The subject is a female in their 70s; a dermatoscopic image of a skin lesion.
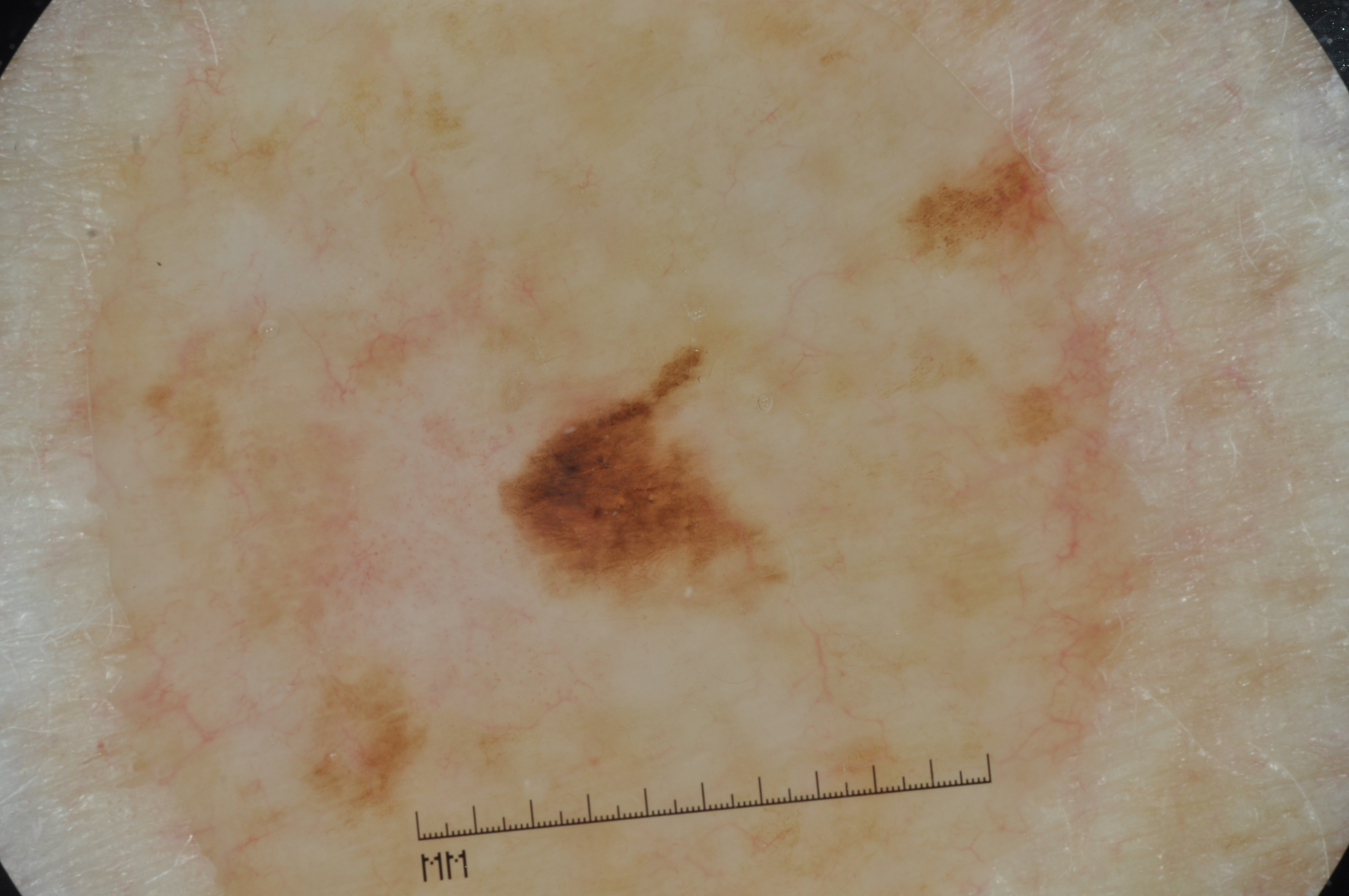On dermoscopy, the lesion shows pigment network and milia-like cysts, with no streaks or negative network.
The lesion is small relative to the field of view.
In (x1, y1, x2, y2) order, the lesion's extent is [498,317,789,615].
Histopathological examination showed a melanoma, a skin cancer.